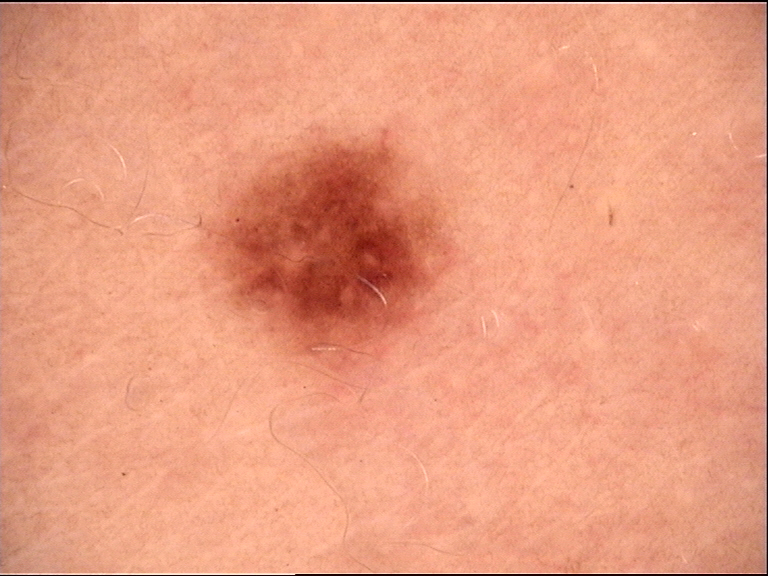image type: dermatoscopy; diagnosis: dysplastic junctional nevus (expert consensus).